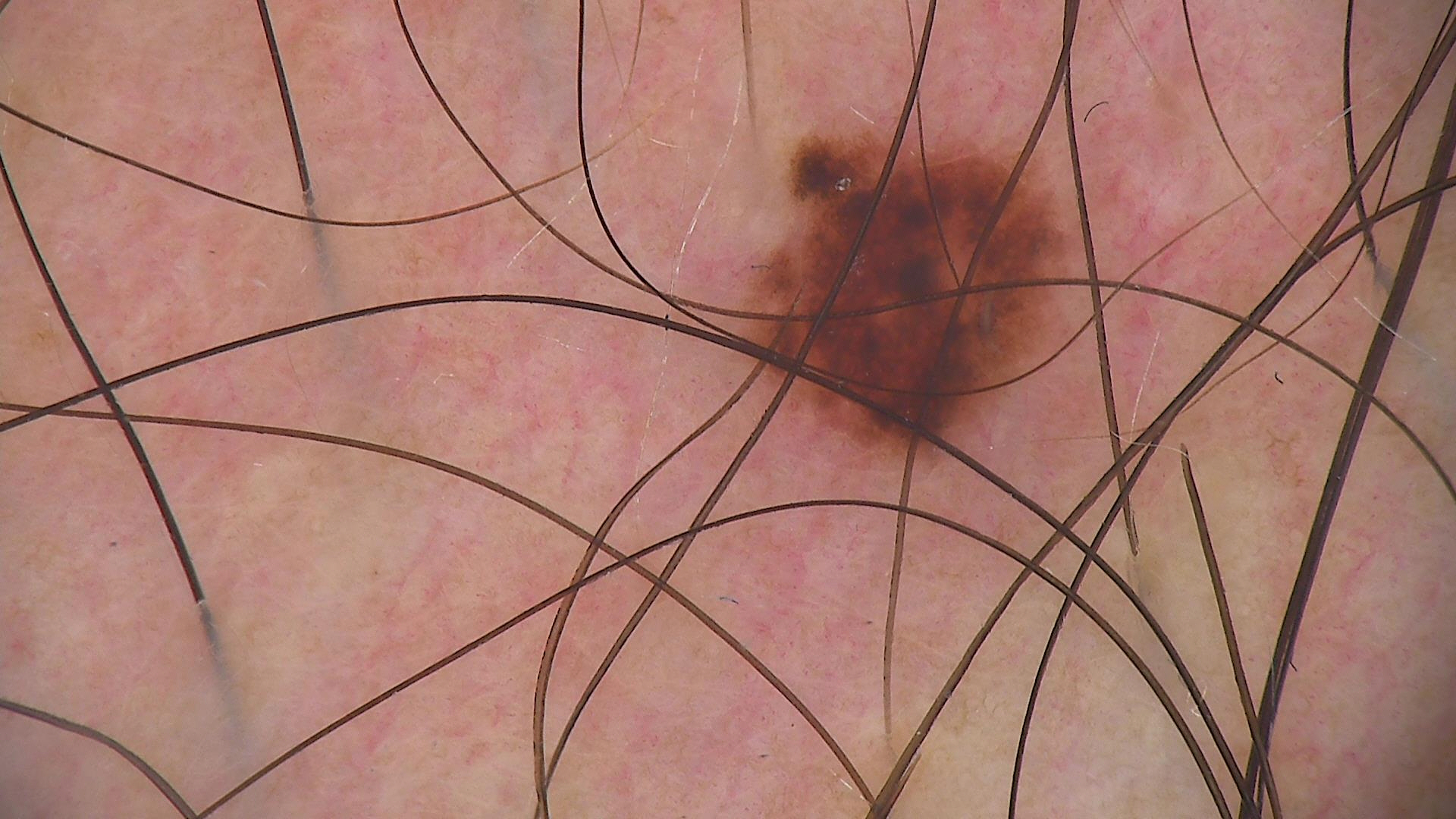image: dermatoscopy
assessment: dysplastic compound nevus (expert consensus)